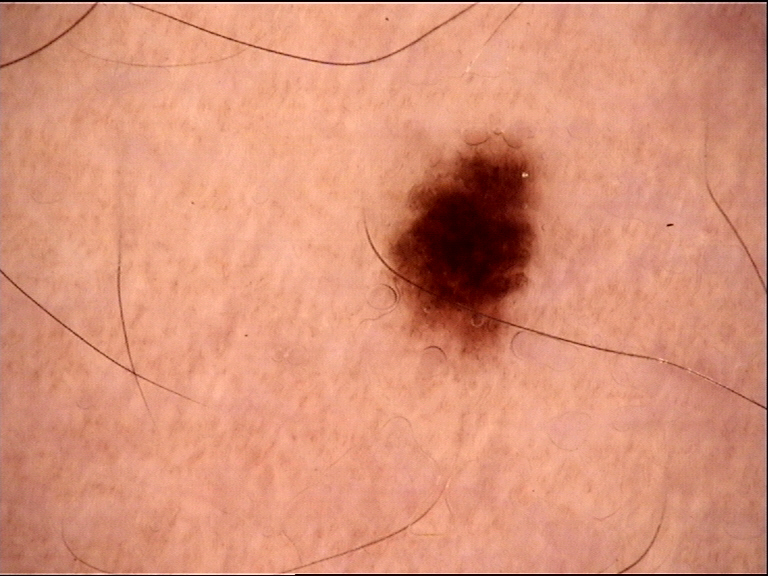subtype — banal | class — junctional nevus (expert consensus).